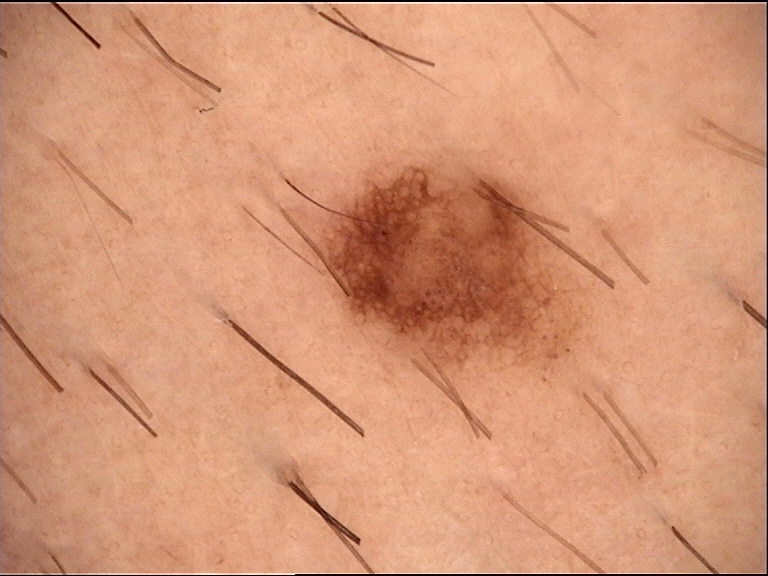diagnosis:
  name: dysplastic junctional nevus
  code: jd
  malignancy: benign
  super_class: melanocytic
  confirmation: expert consensus